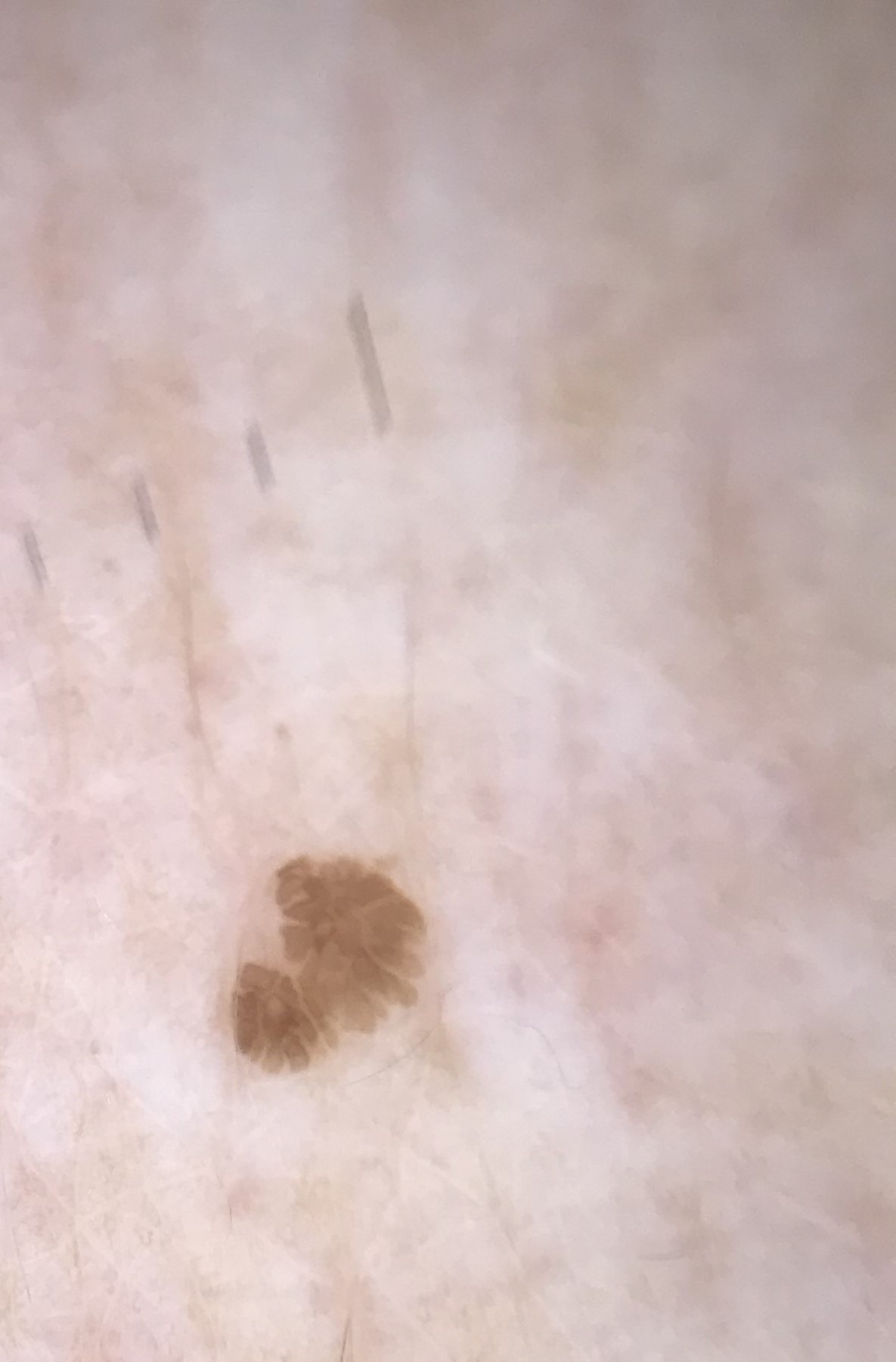imaging = dermoscopy; lesion type = keratinocytic; diagnosis = seborrheic keratosis (expert consensus).